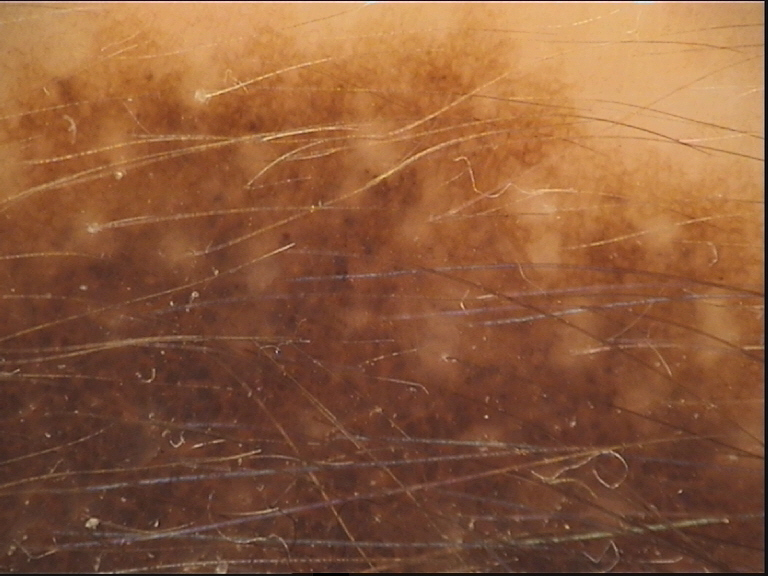Findings:
* diagnostic label · congenital compound nevus (expert consensus)